A dermoscopic close-up of a skin lesion.
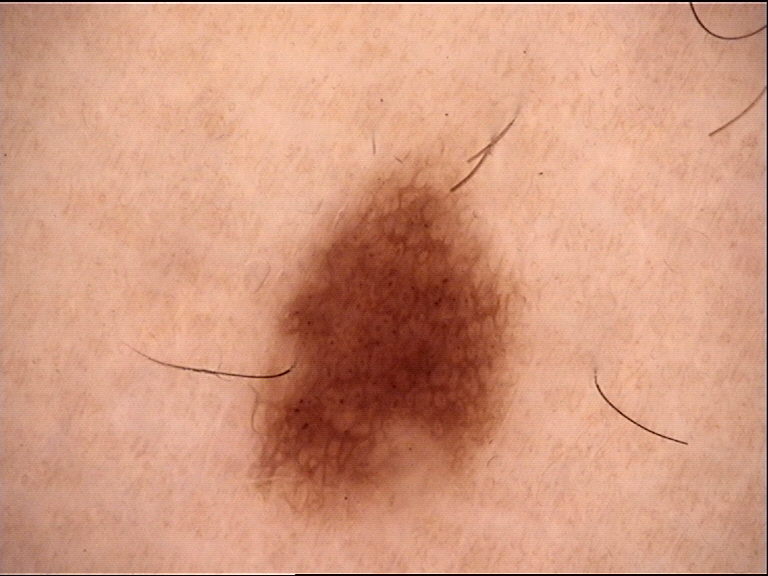Q: How is the lesion classified?
A: banal
Q: What was the diagnostic impression?
A: junctional nevus (expert consensus)